A skin lesion imaged with a dermatoscope.
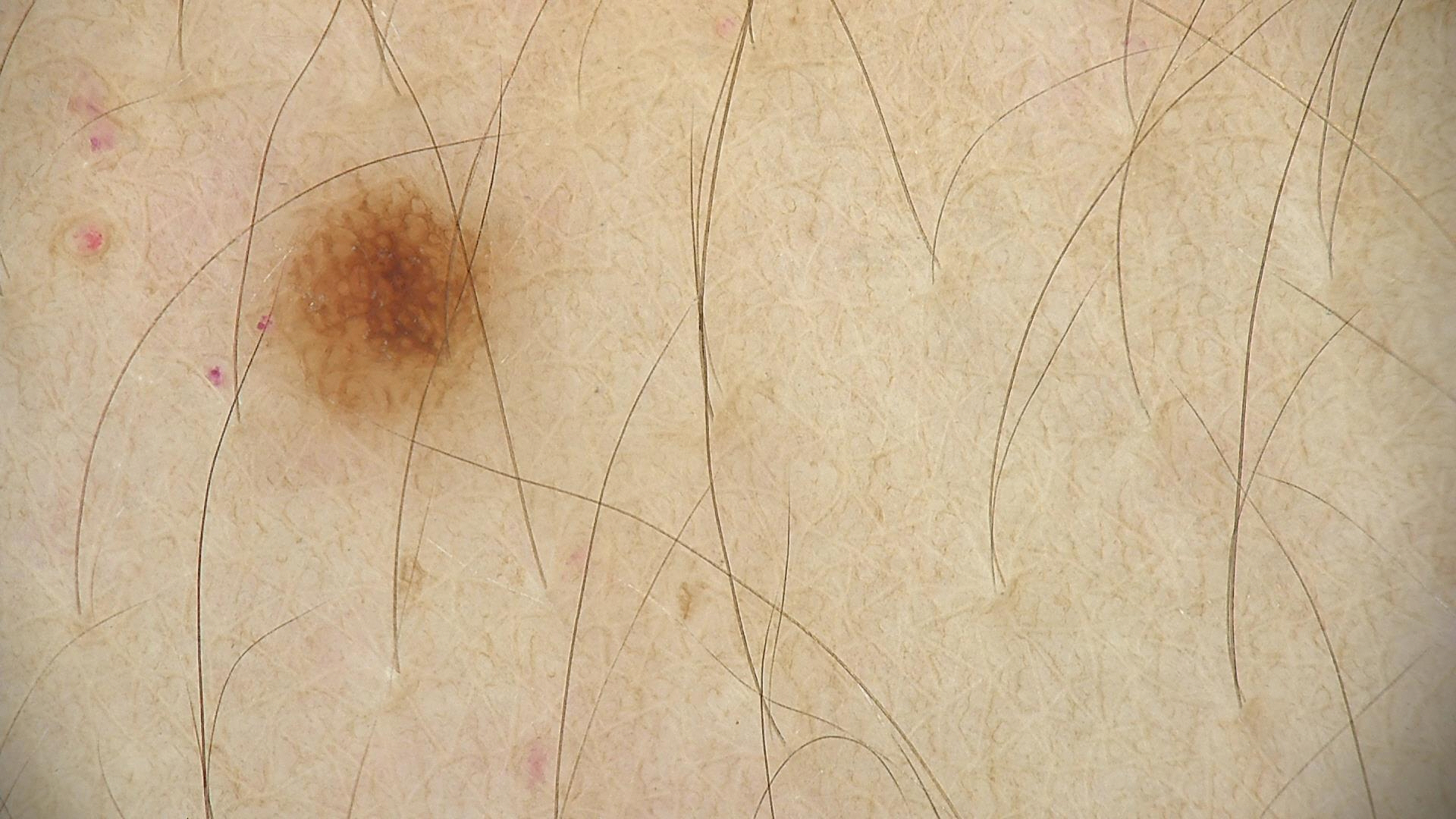Conclusion:
The diagnosis was a dysplastic junctional nevus.